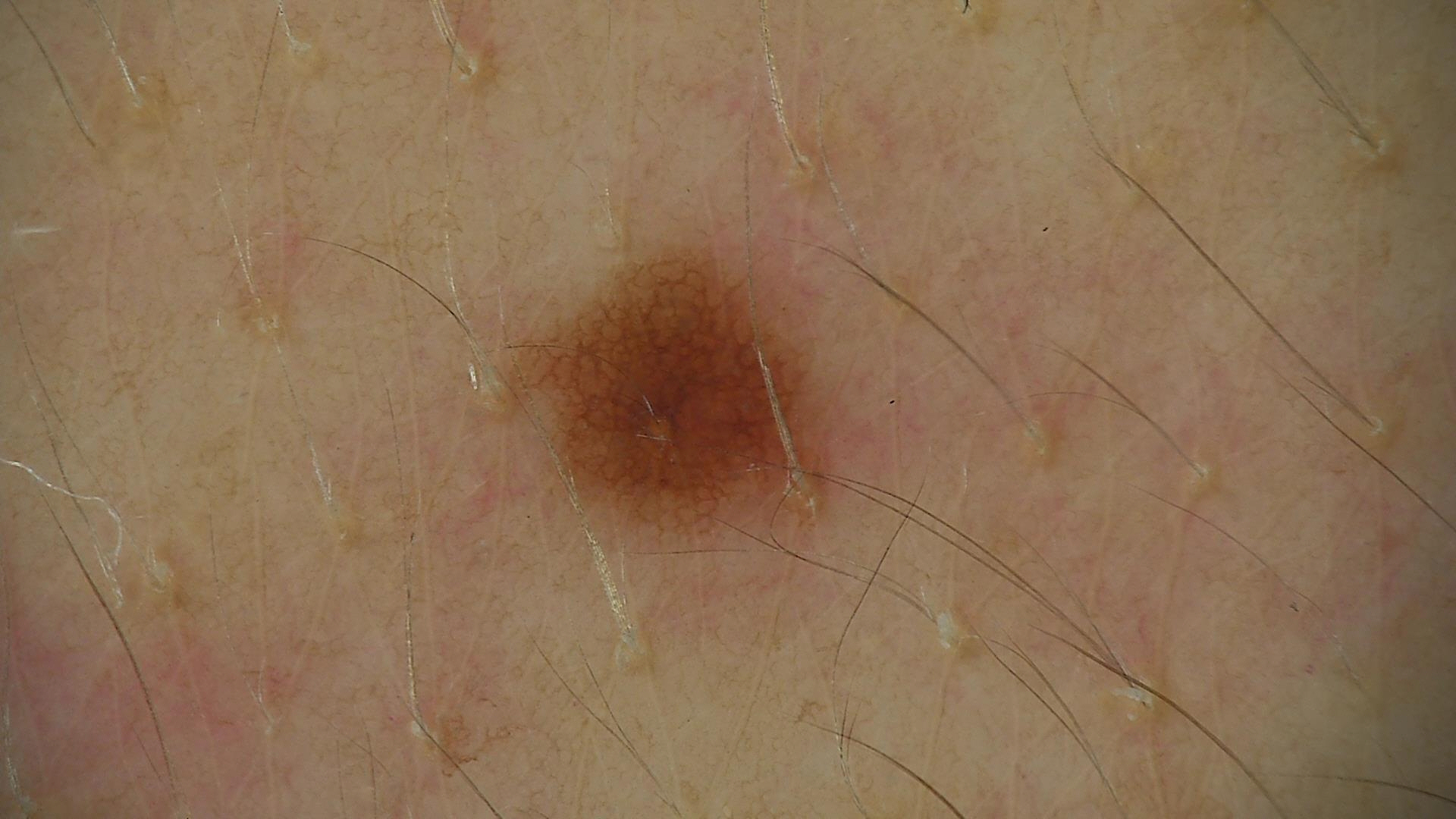diagnostic label: dysplastic junctional nevus (expert consensus).